Dermoscopy of a skin lesion: 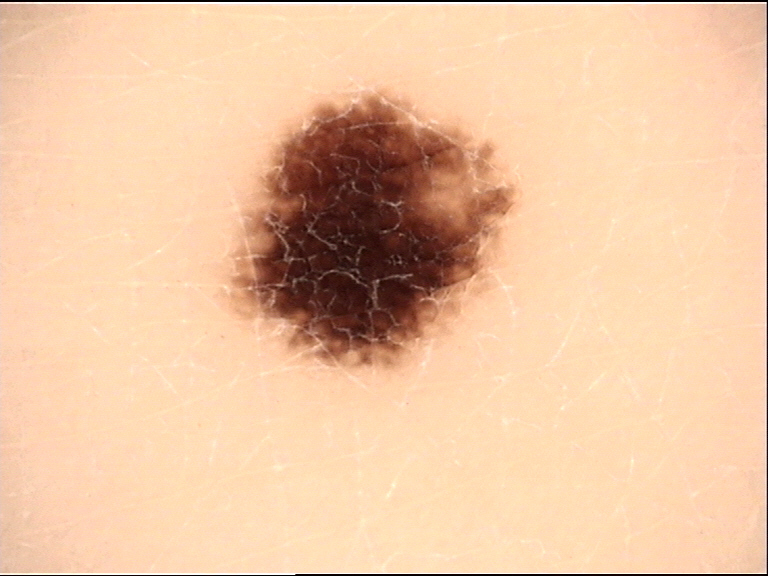{"diagnosis": {"name": "acral dysplastic junctional nevus", "code": "ajd", "malignancy": "benign", "super_class": "melanocytic", "confirmation": "expert consensus"}}